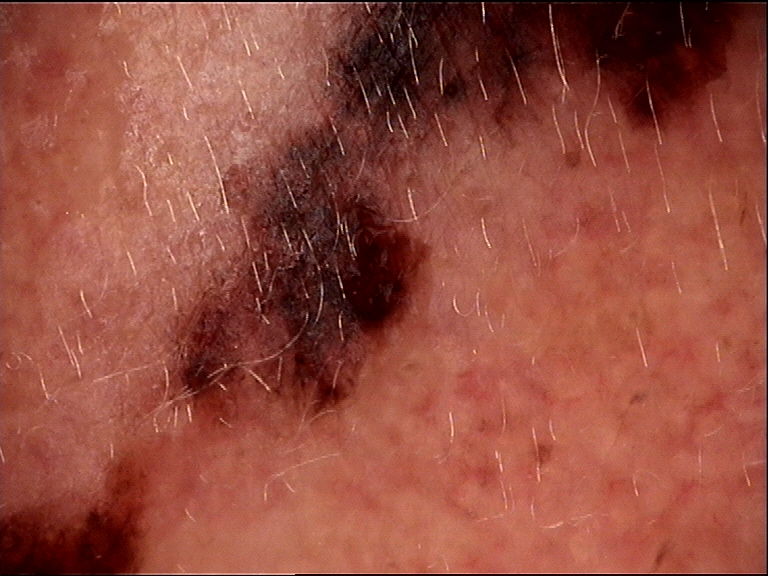Q: What did the workup show?
A: melanoma (biopsy-proven)